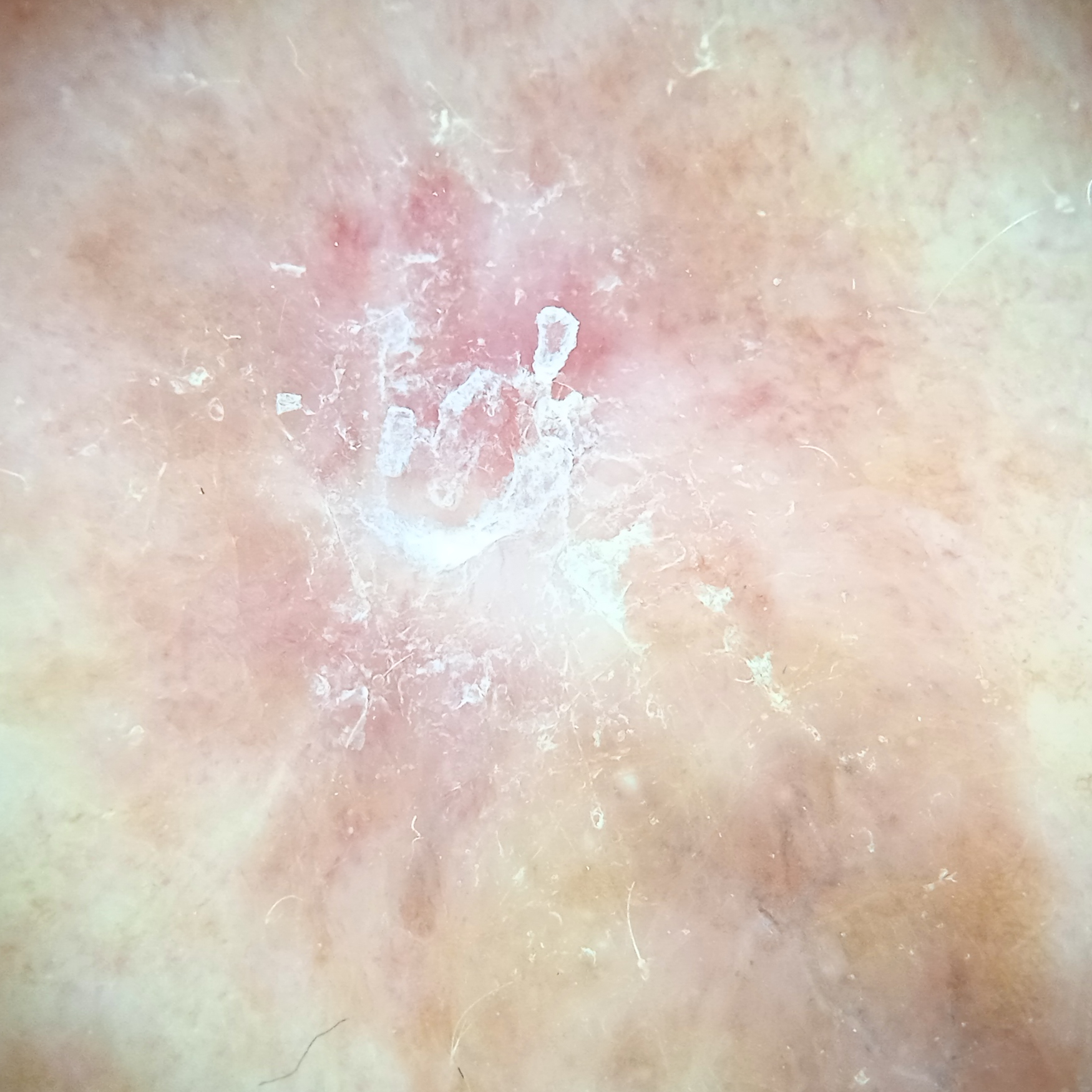Case summary:
A skin lesion imaged with a dermatoscope. A male subject 62 years of age. Collected as part of a research study, without a referral diagnosis. Located on the back. The lesion is about 13.8 mm across.
Conclusion:
Dermatologist review favored a squamous cell carcinoma.